A dermoscopic photograph of a skin lesion:
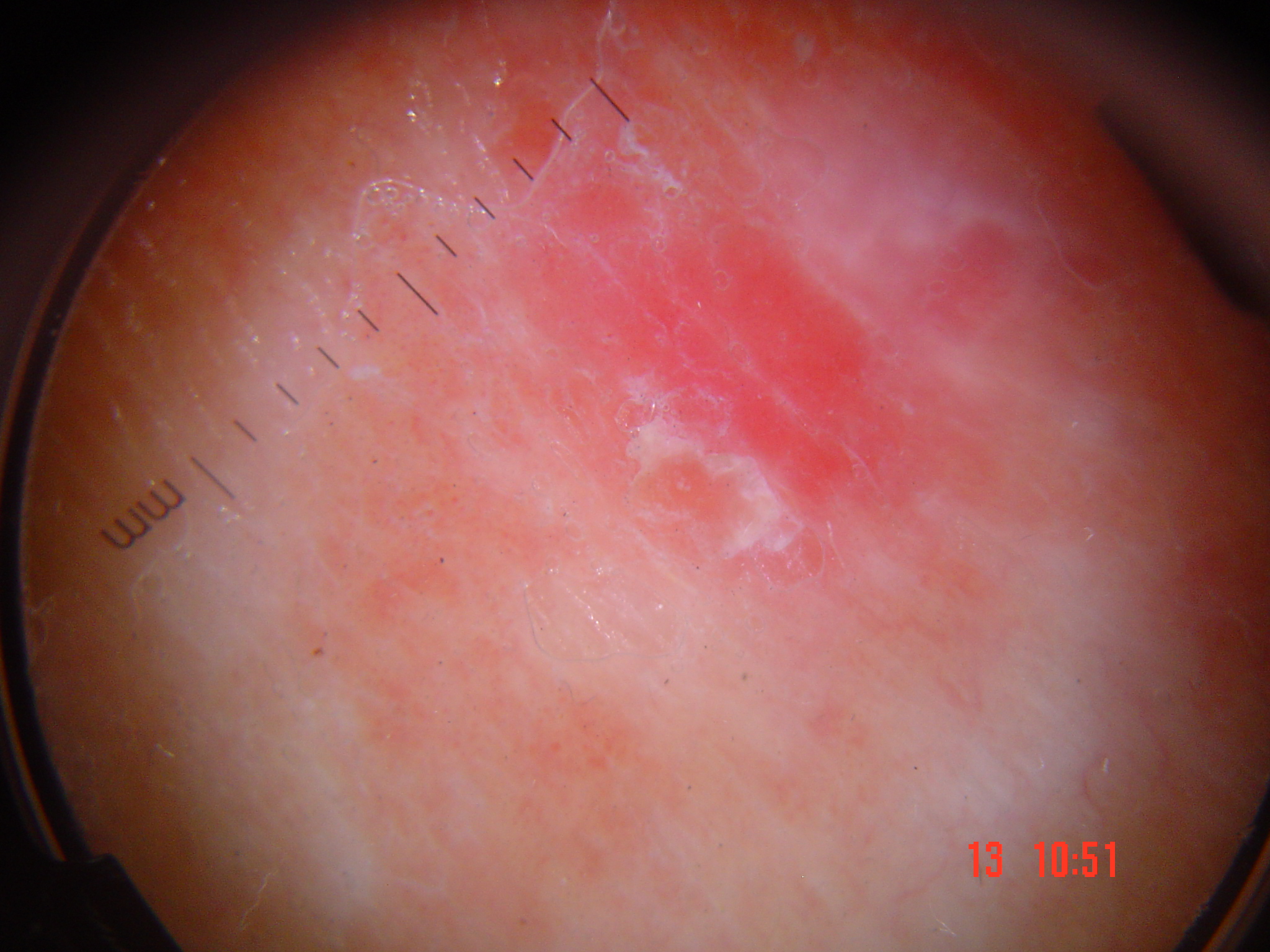diagnosis:
  name: Bowen's disease
  code: bd
  malignancy: malignant
  super_class: non-melanocytic
  confirmation: histopathology